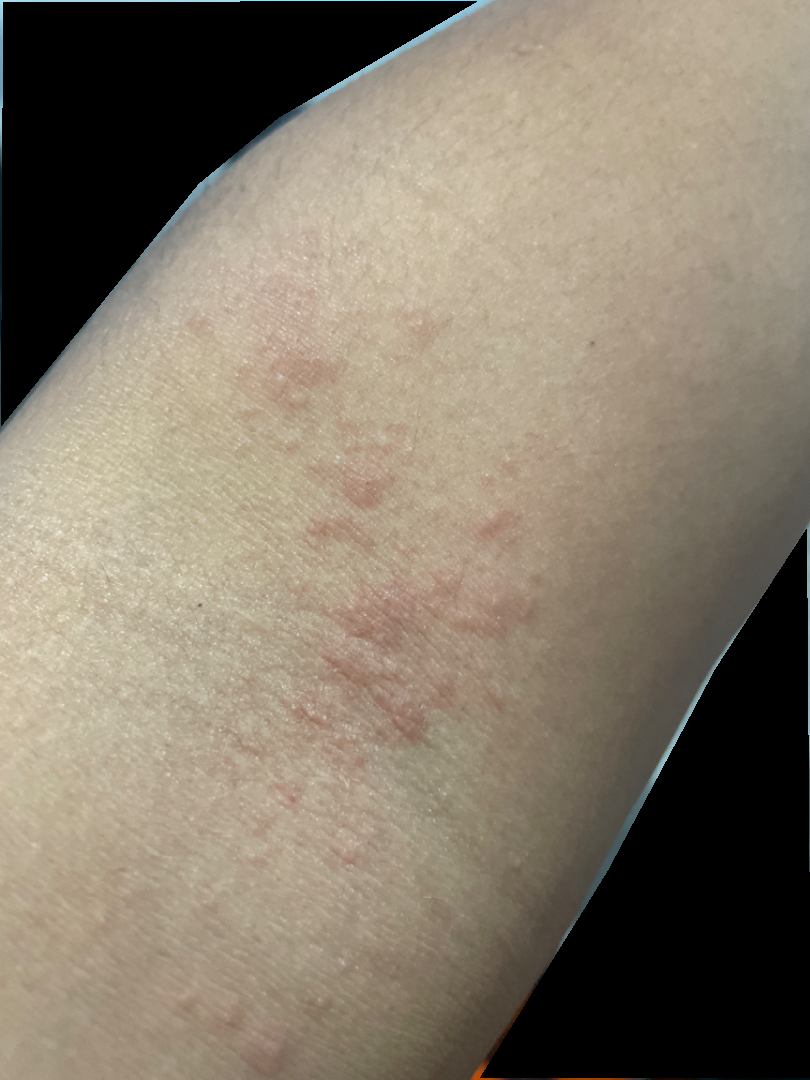Clinical context:
The lesion is described as raised or bumpy. Self-categorized by the patient as acne. The subject is a male aged 18–29. Reported duration is less than one week. The arm and back of the hand are involved. Fitzpatrick skin type II. Close-up view. The patient reported no systemic symptoms.
Assessment:
Most likely Eczema; with consideration of Allergic Contact Dermatitis.